A dermoscopy image of a single skin lesion: 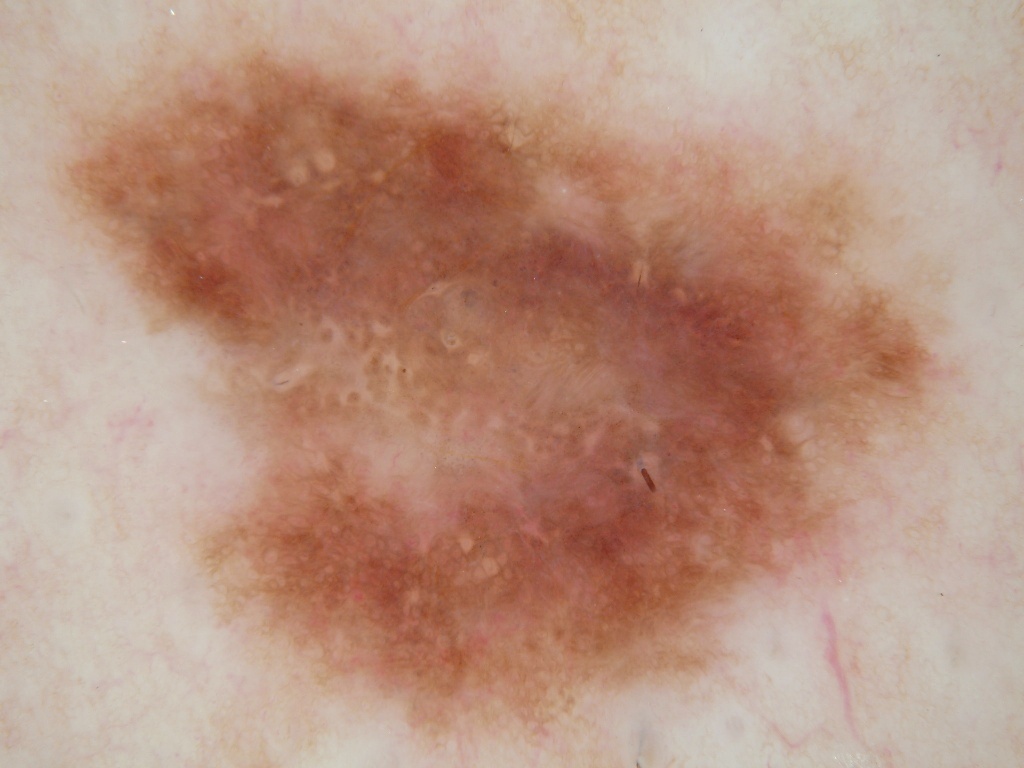Dermoscopically, the lesion shows milia-like cysts, pigment network, and negative network, with no globules or streaks. The lesion is bounded by left=53, top=16, right=956, bottom=740. Diagnosed as a melanocytic nevus.